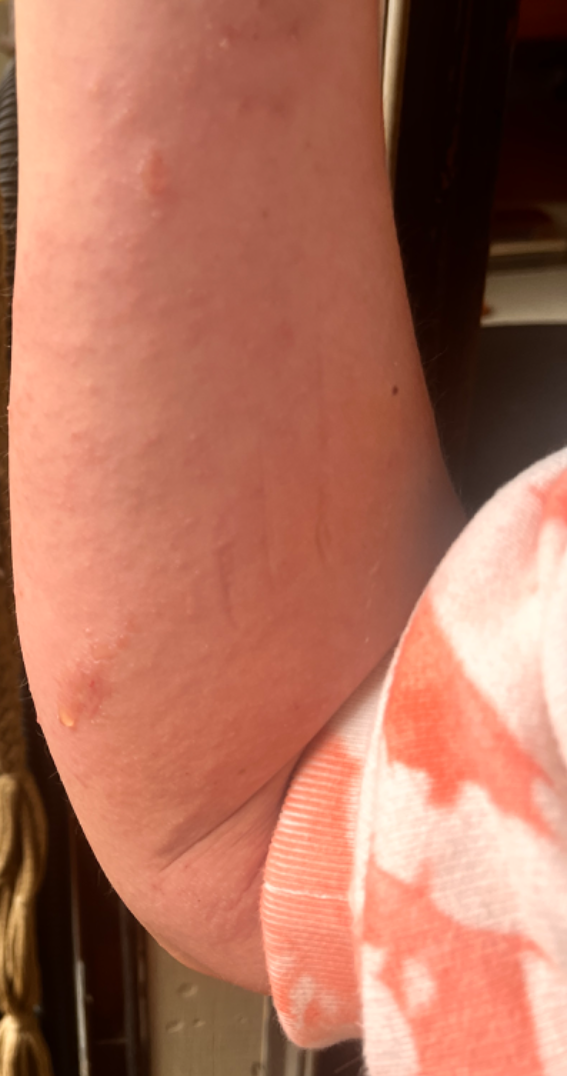The reviewer was unable to grade this case for skin condition.